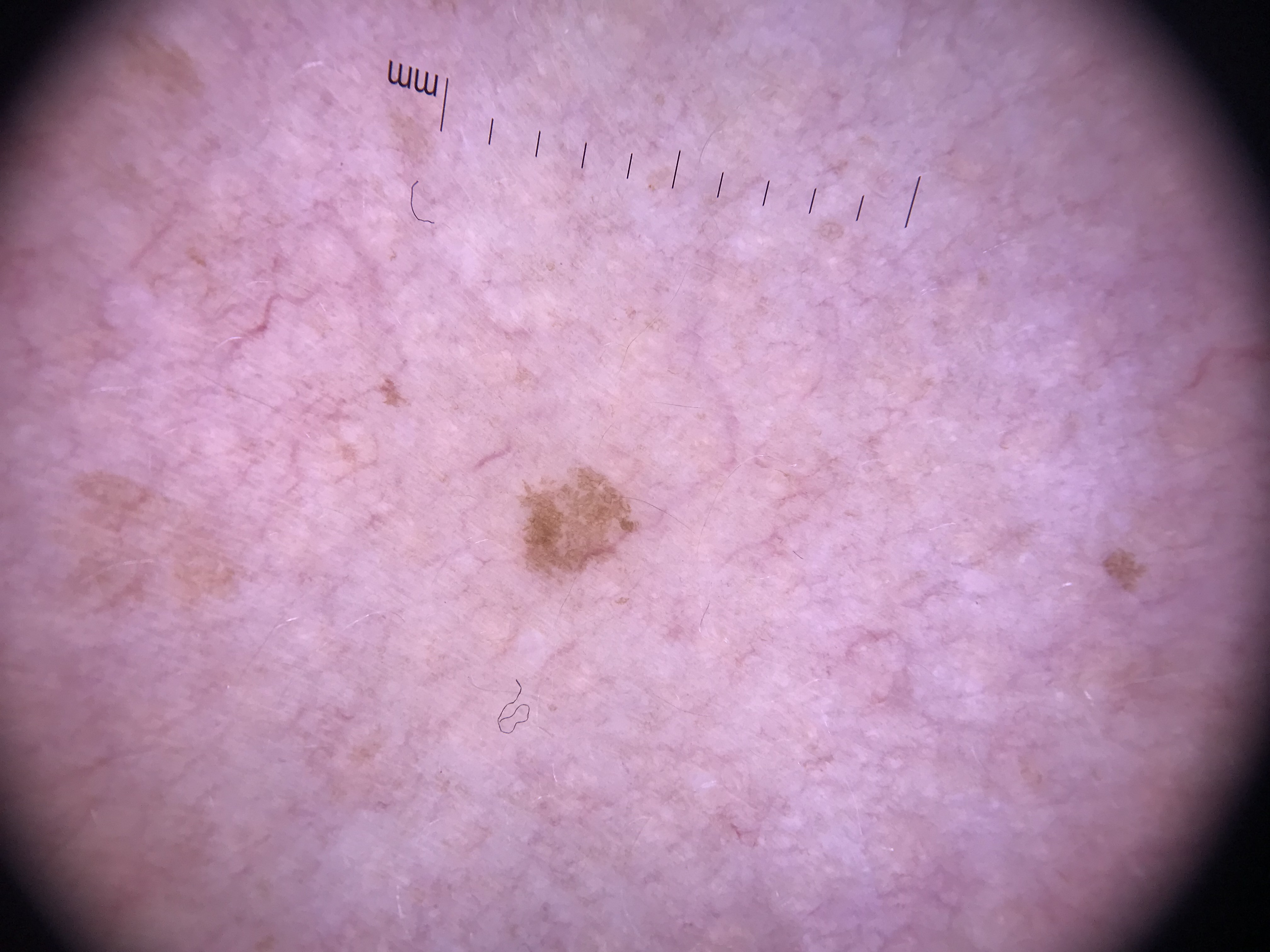Conclusion:
The diagnostic label was a benign lesion — a seborrheic keratosis.